A dermoscopic image of a skin lesion: 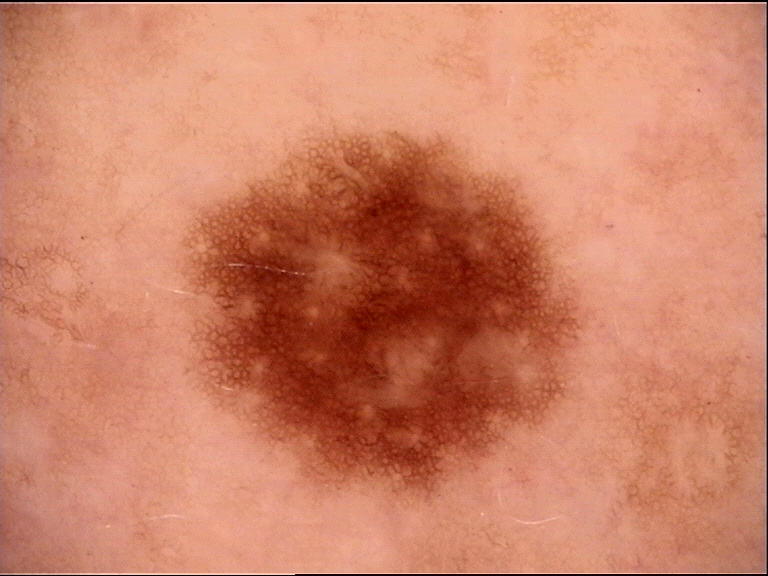Impression: Classified as a dysplastic junctional nevus.